A dermoscopic close-up of a skin lesion: 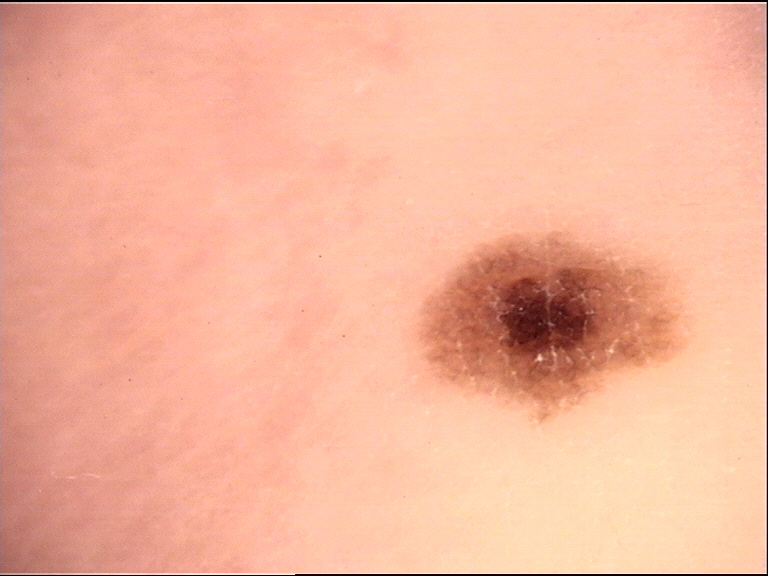  diagnosis:
    name: dysplastic junctional nevus
    code: jd
    malignancy: benign
    super_class: melanocytic
    confirmation: expert consensus